A skin lesion imaged with a dermatoscope.
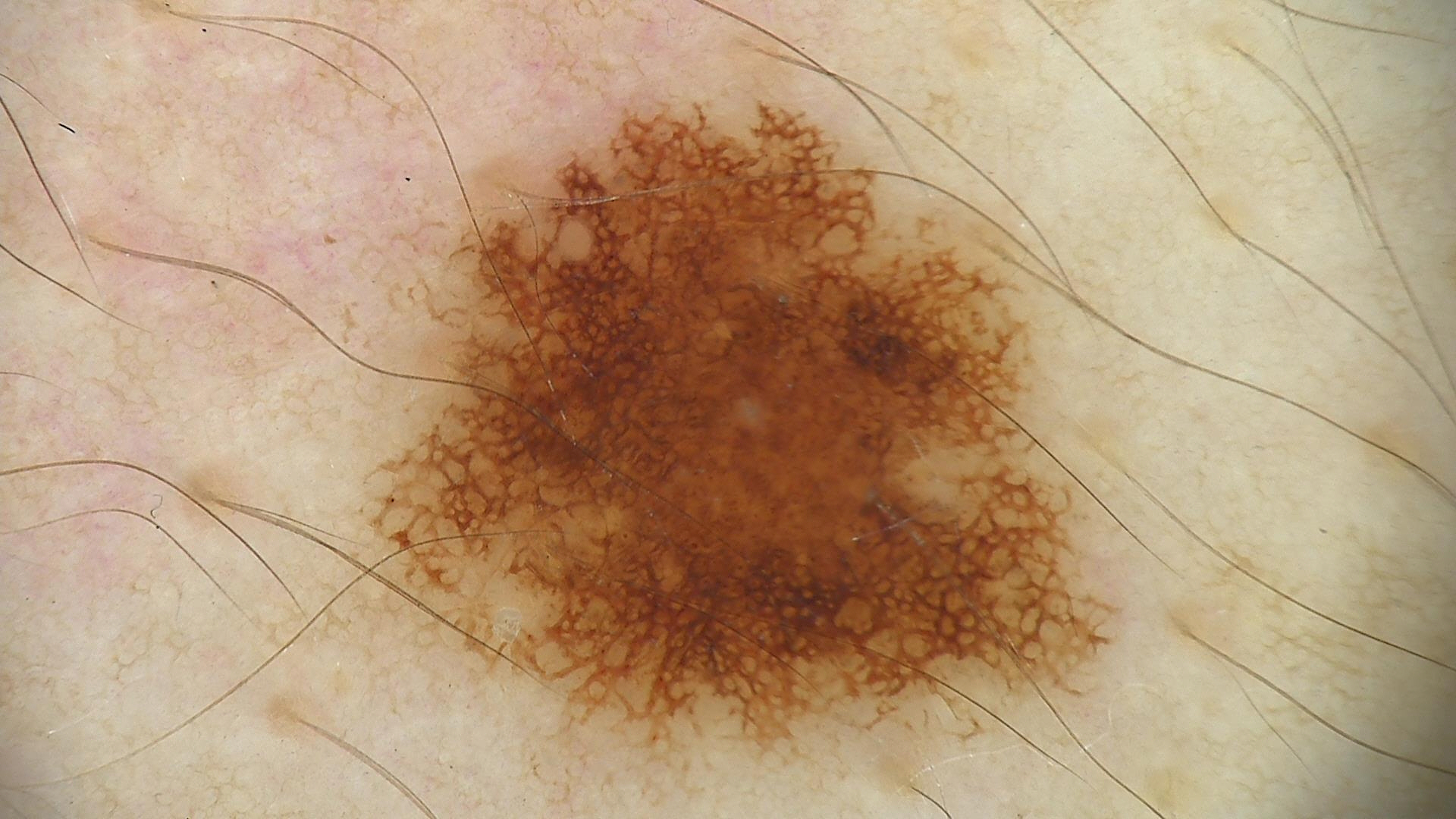class: dysplastic junctional nevus (expert consensus).